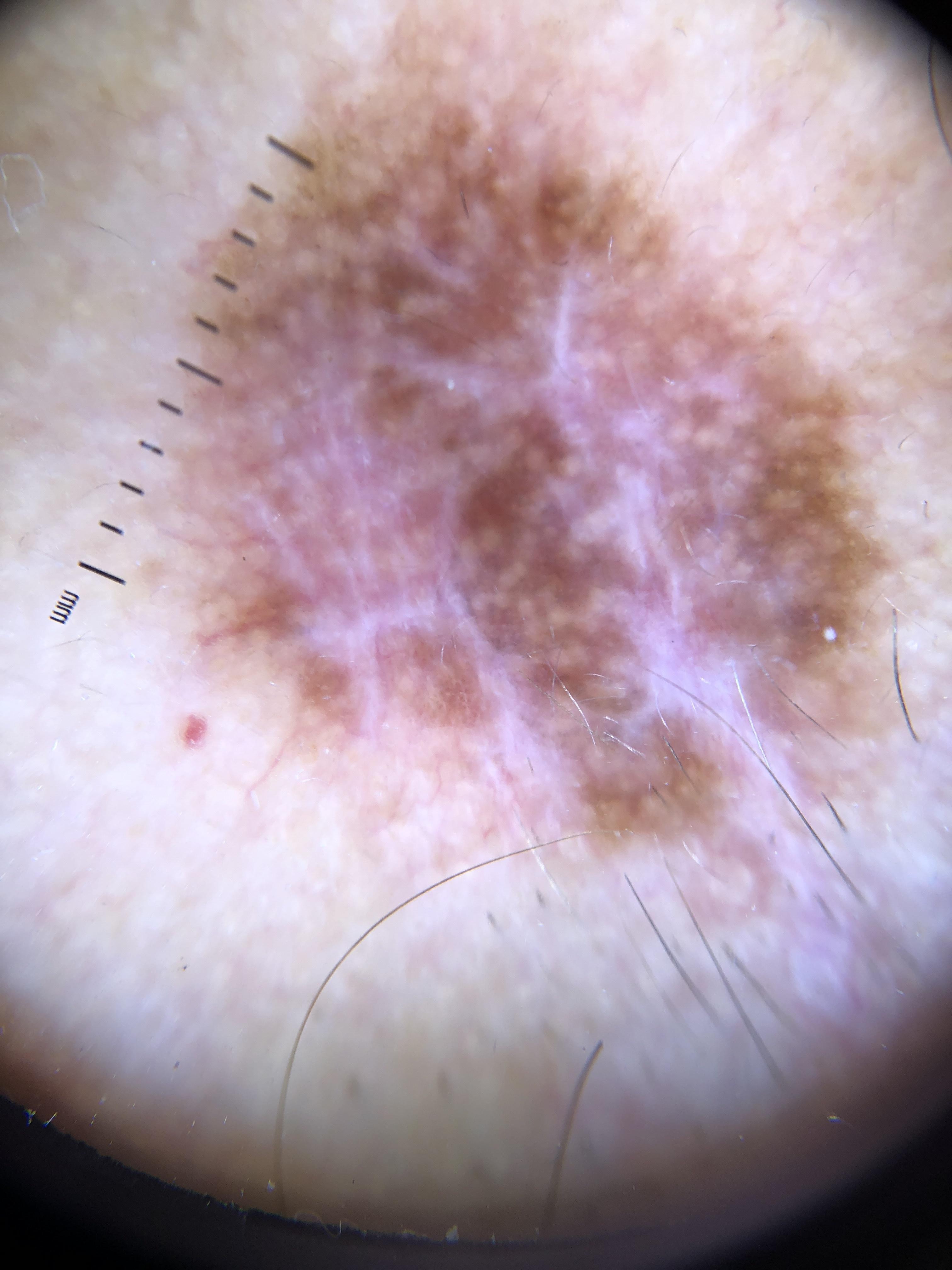The biopsy diagnosis was a melanoma.